The photograph is a close-up of the affected area · skin tone: Fitzpatrick III; non-clinician graders estimated a Monk Skin Tone of 4: 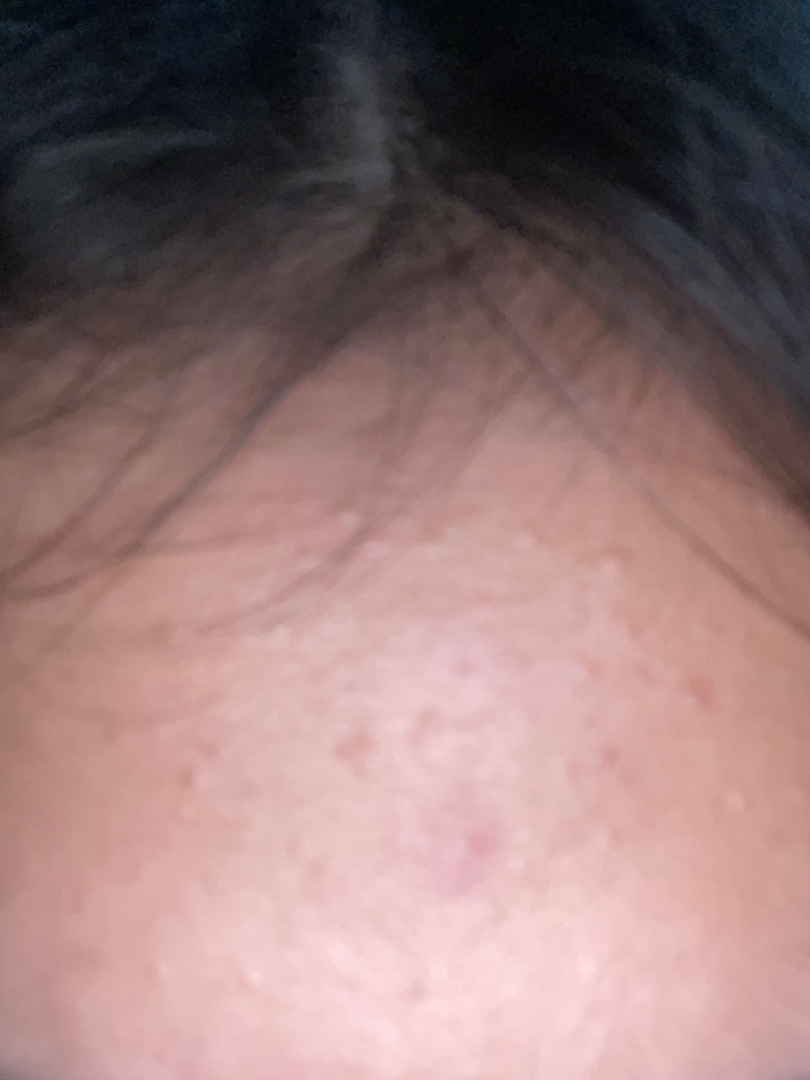Assessment:
On remote dermatologist review, in keeping with Acne.